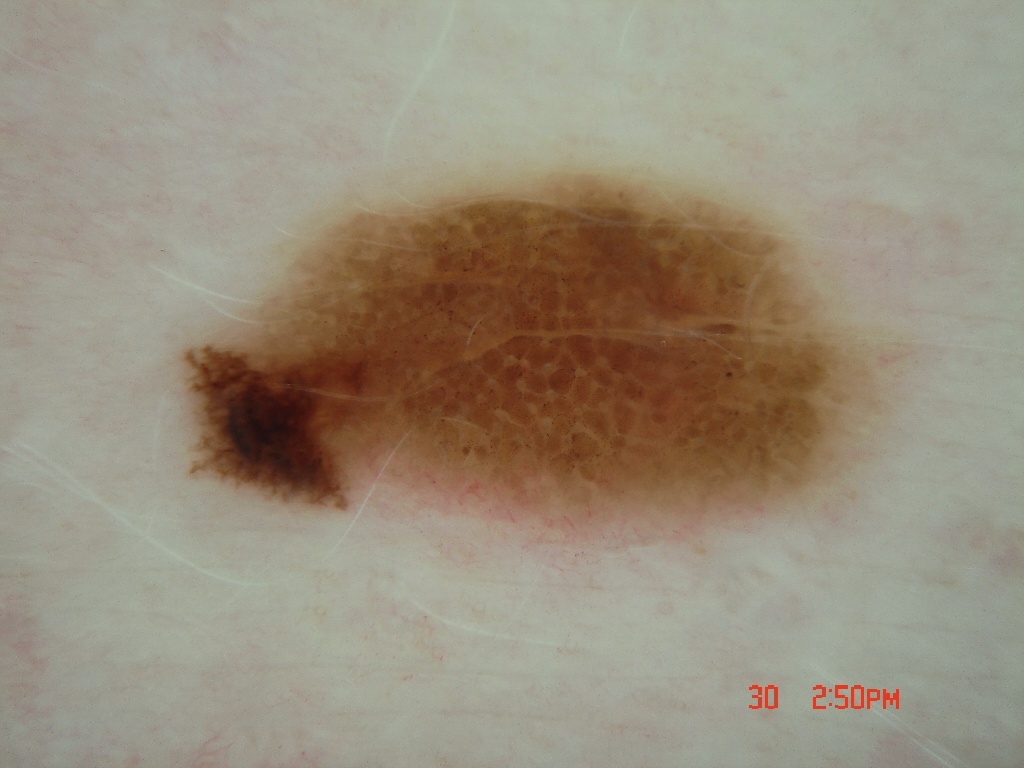Summary: A skin lesion imaged with a dermatoscope. As (left, top, right, bottom), the lesion is bounded by (173, 170, 902, 537). Dermoscopic assessment notes globules and streaks. Assessment: Clinically diagnosed as a benign skin lesion.